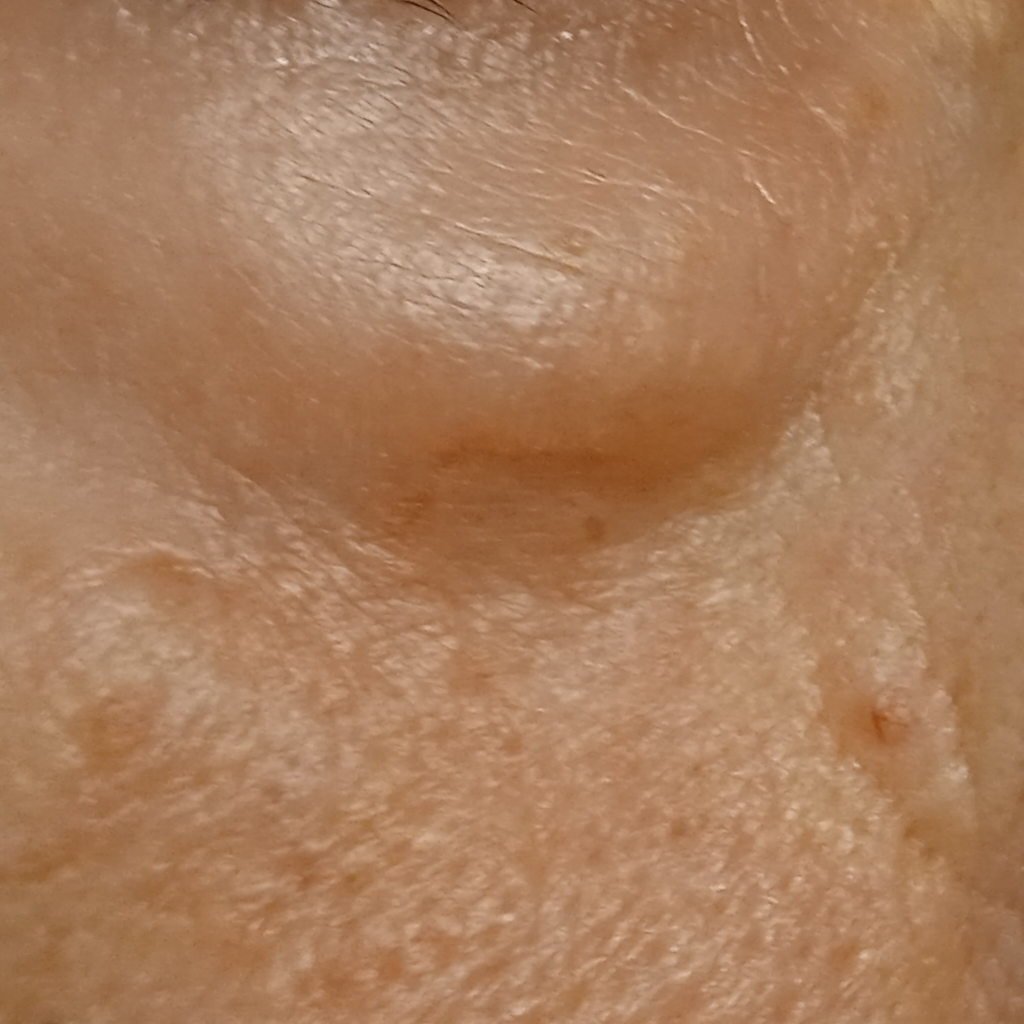A female patient aged 68. A clinical photograph of a skin lesion. The patient says their skin tans without first burning. Dermatologist review favored a basal cell carcinoma.